A dermoscopy image of a single skin lesion.
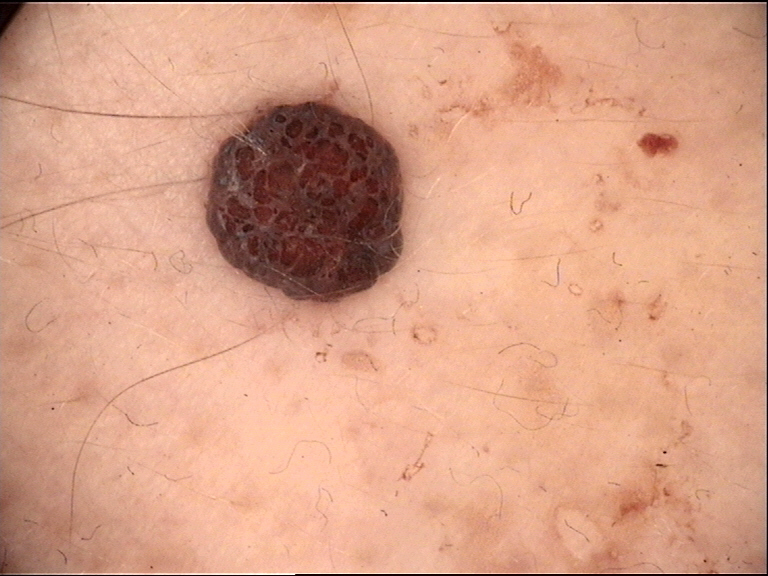category = banal; label = dermal nevus (expert consensus).